A skin lesion imaged with a dermatoscope.
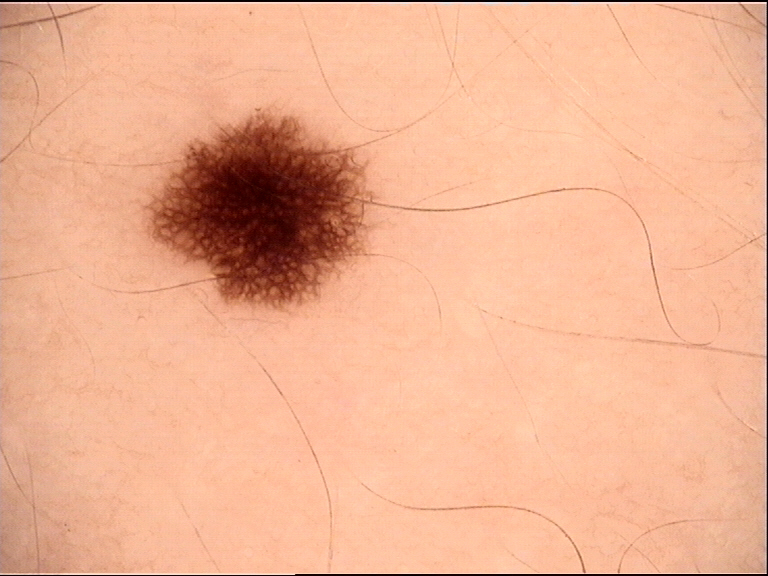category=banal | diagnostic label=junctional nevus (expert consensus).